An image taken at an angle · male contributor, age 50–59 · the back of the hand is involved — 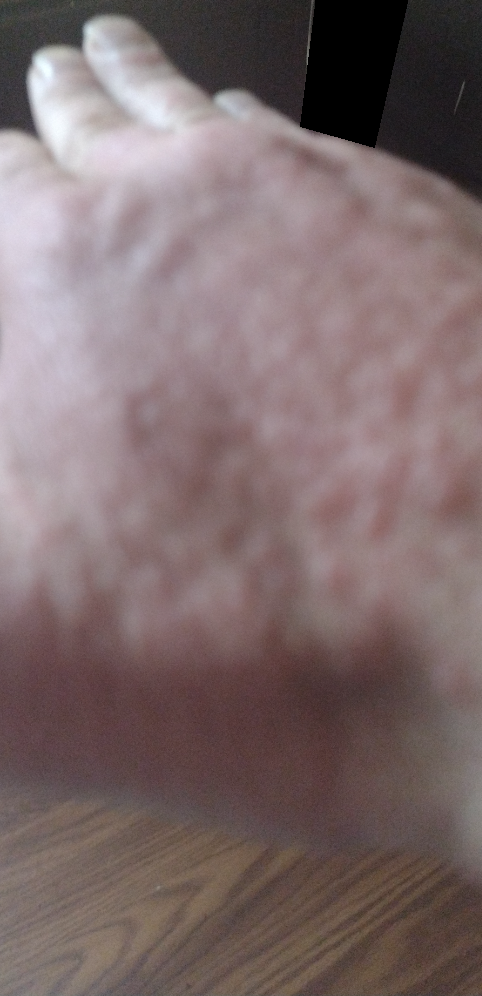Q: What was the assessment?
A: could not be assessed
Q: Patient's own categorization?
A: a rash
Q: Any systemic symptoms?
A: joint pain and fatigue
Q: How long has this been present?
A: less than one week
Q: Texture?
A: raised or bumpy
Q: Reported symptoms?
A: pain, burning, bothersome appearance and itching